Symptoms reported: bothersome appearance, enlargement and itching. This is a close-up image. The affected area is the leg. Self-categorized by the patient as a rash. The condition has been present for one to four weeks. No relevant systemic symptoms. Texture is reported as rough or flaky: 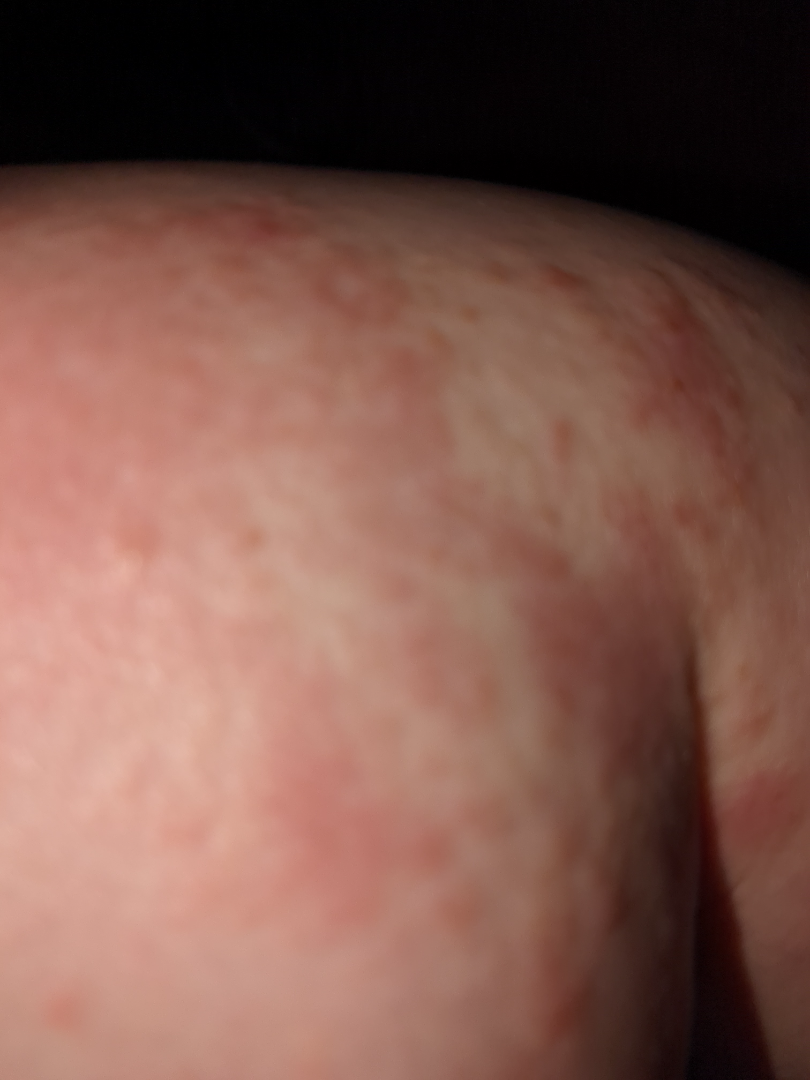<case>
  <assessment>indeterminate from the photograph</assessment>
</case>